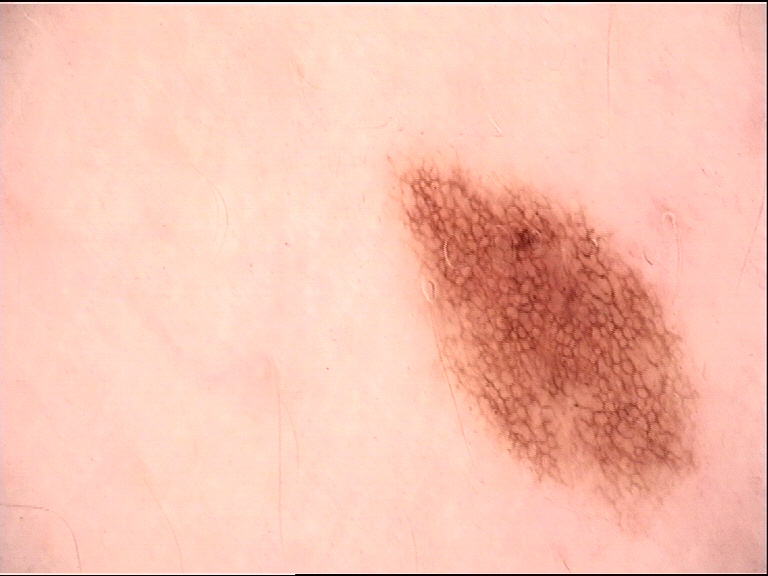image: dermatoscopy; label: dysplastic junctional nevus (expert consensus).